The contributor reports the condition has been present for one to four weeks; the affected area is the leg and top or side of the foot; this image was taken at a distance; reported lesion symptoms include burning, itching and bothersome appearance; no associated systemic symptoms reported; texture is reported as rough or flaky and flat.
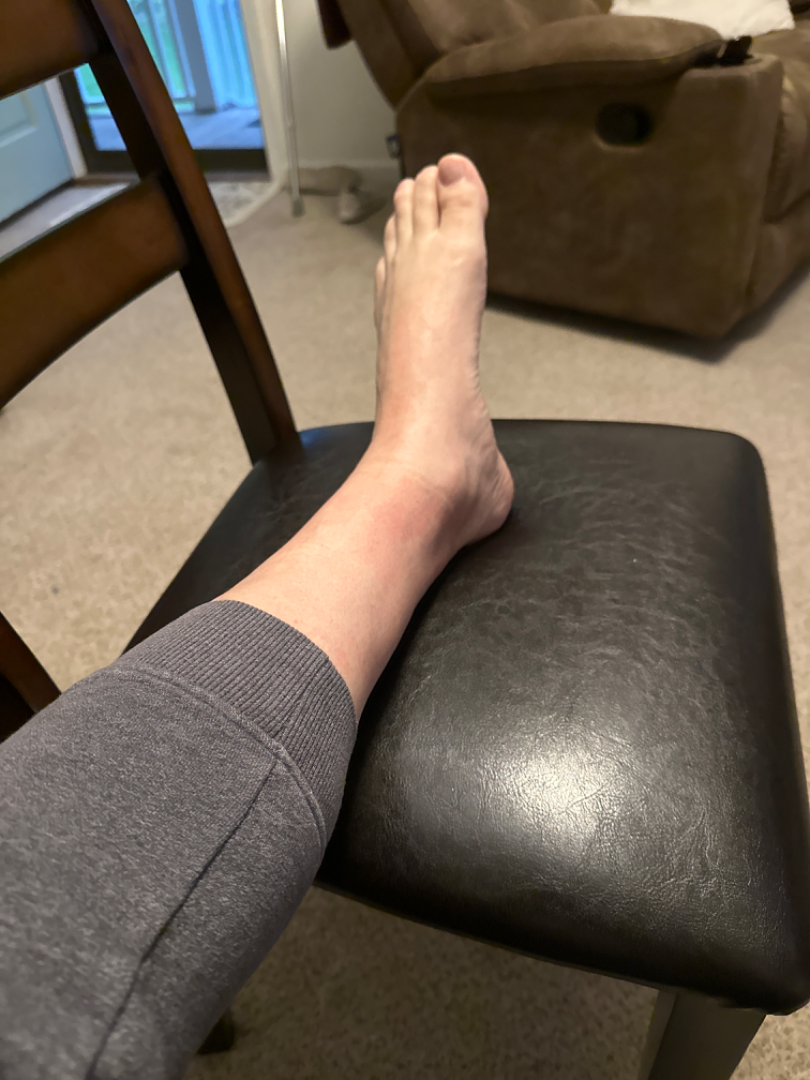{"assessment": "ungradable on photographic review"}